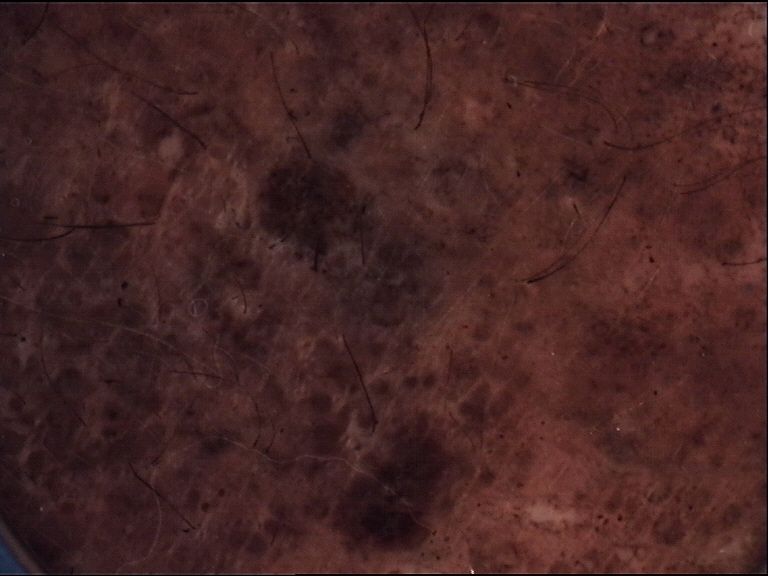A dermoscopic photograph of a skin lesion.
Classified as a banal lesion — a congenital compound nevus.